The photograph is a close-up of the affected area; the patient indicates burning, bothersome appearance and enlargement; self-categorized by the patient as a rash; texture is reported as flat and rough or flaky; male contributor, age 18–29; located on the arm, head or neck and front of the torso; the condition has been present for more than one year.
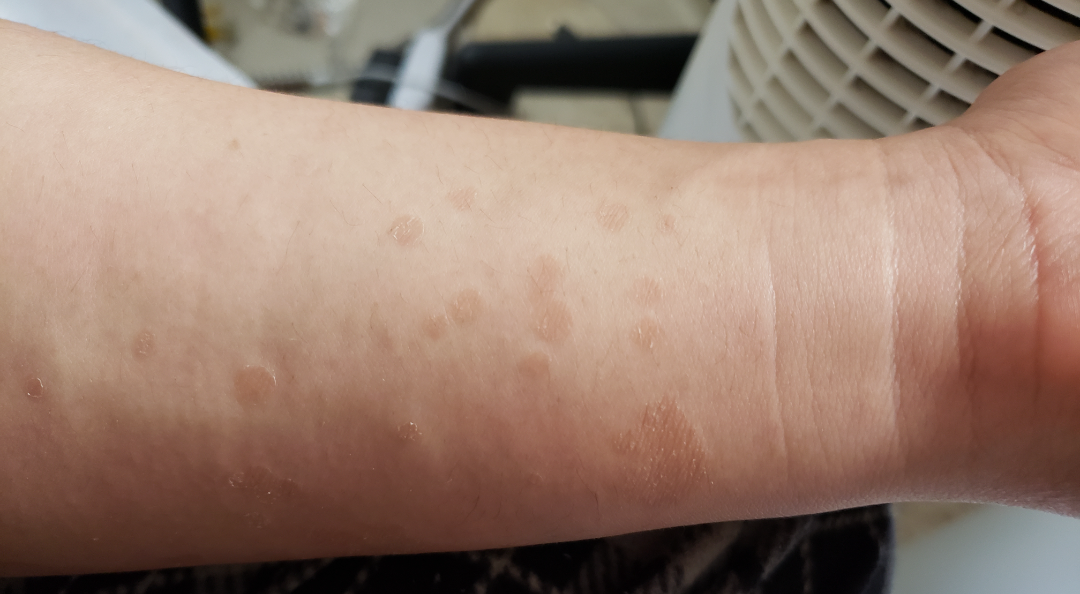Notes:
• differential diagnosis — Psoriasis (0.32); Syphilis (0.32); Tinea Versicolor (0.27); Pityriasis rosea (0.09)